A smartphone photograph of a skin lesion; a patient age 60 — 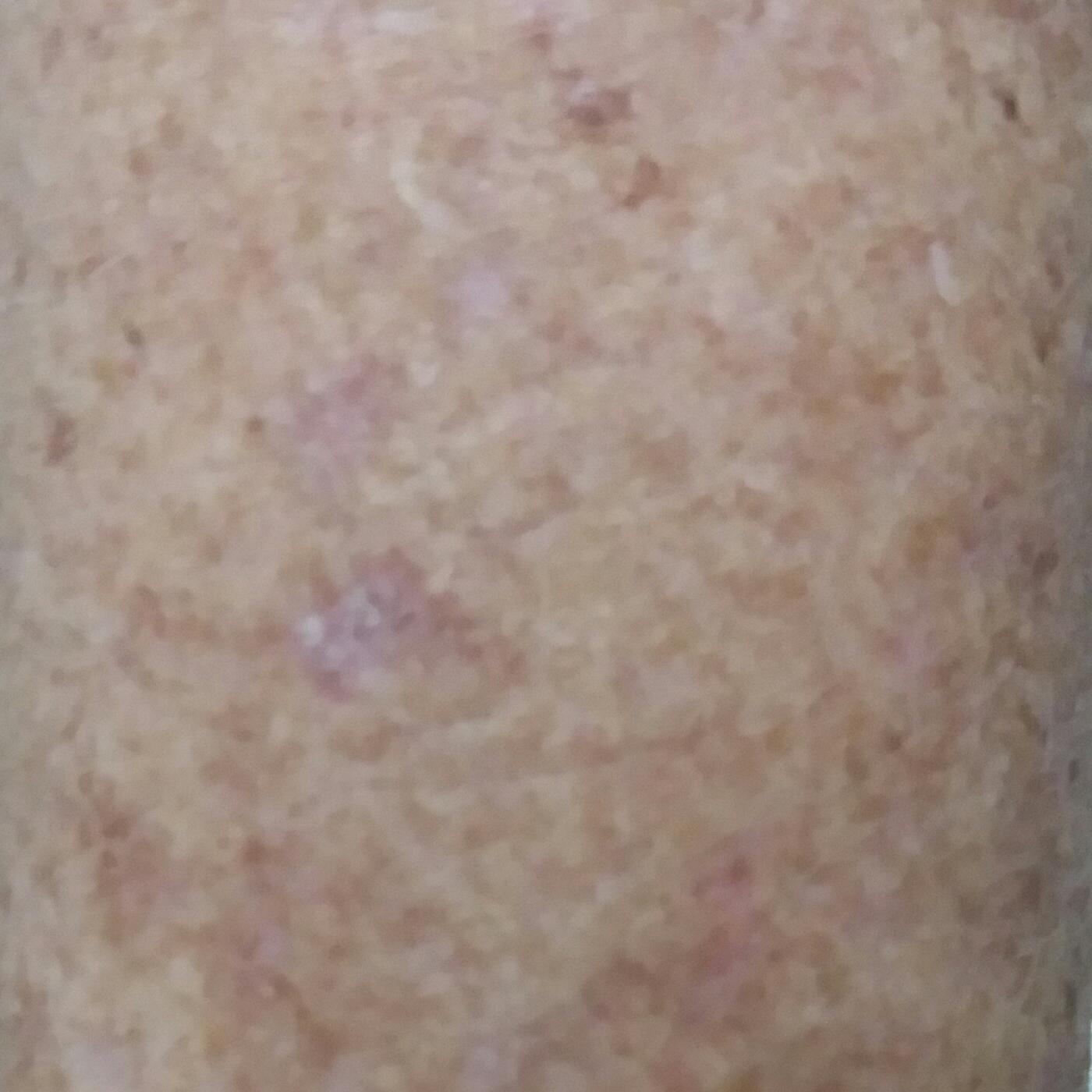{"symptoms": {"present": ["itching"], "absent": ["growth"]}, "diagnosis": {"name": "actinic keratosis", "code": "ACK", "malignancy": "indeterminate", "confirmation": "clinical consensus"}}